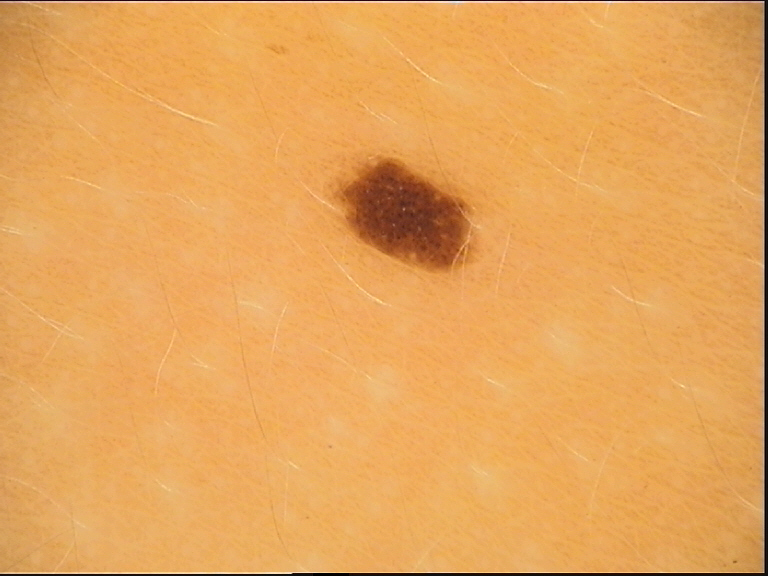The diagnosis was a dysplastic junctional nevus.